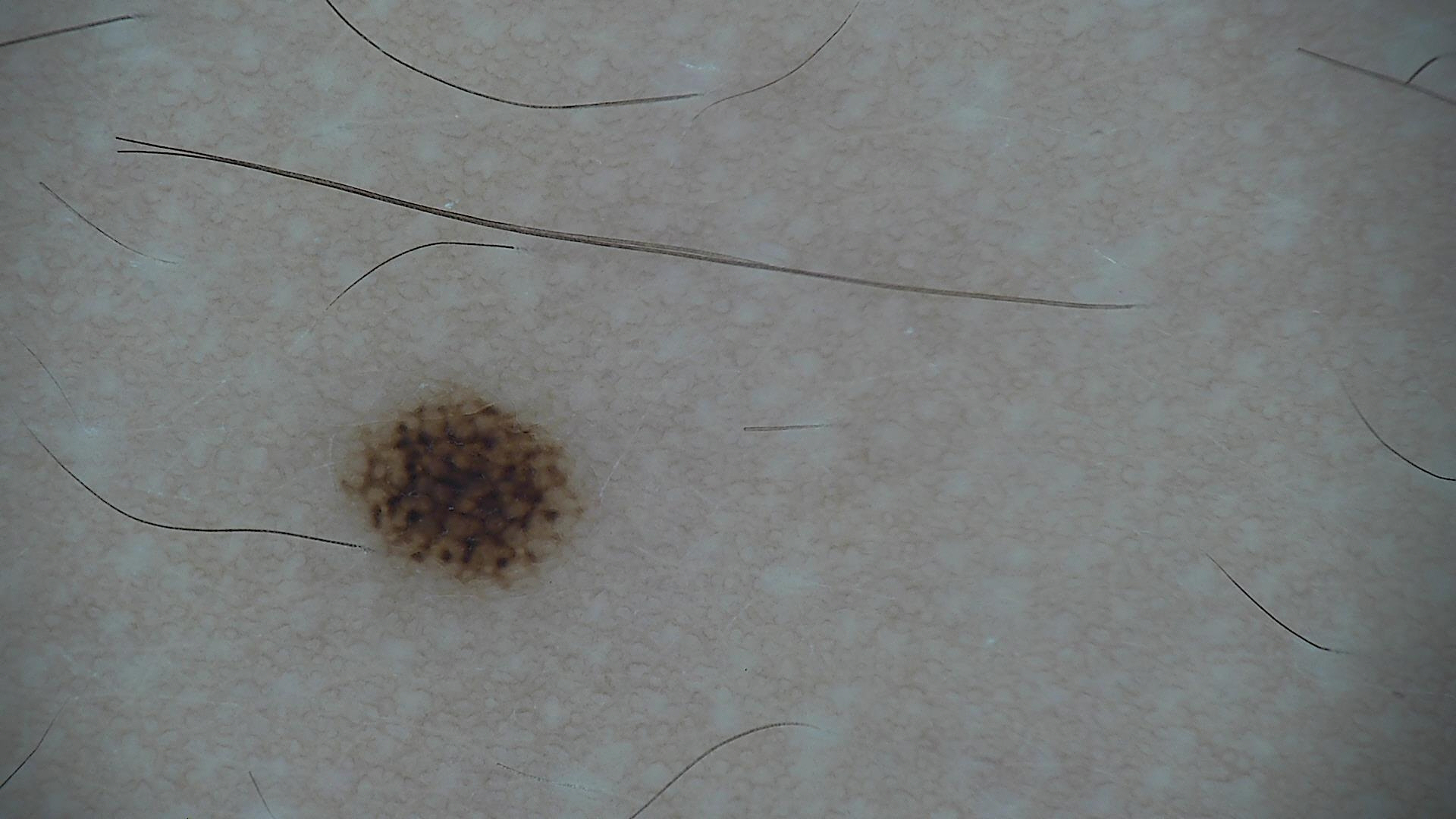A dermoscopy image of a single skin lesion. Diagnosed as a dysplastic junctional nevus.